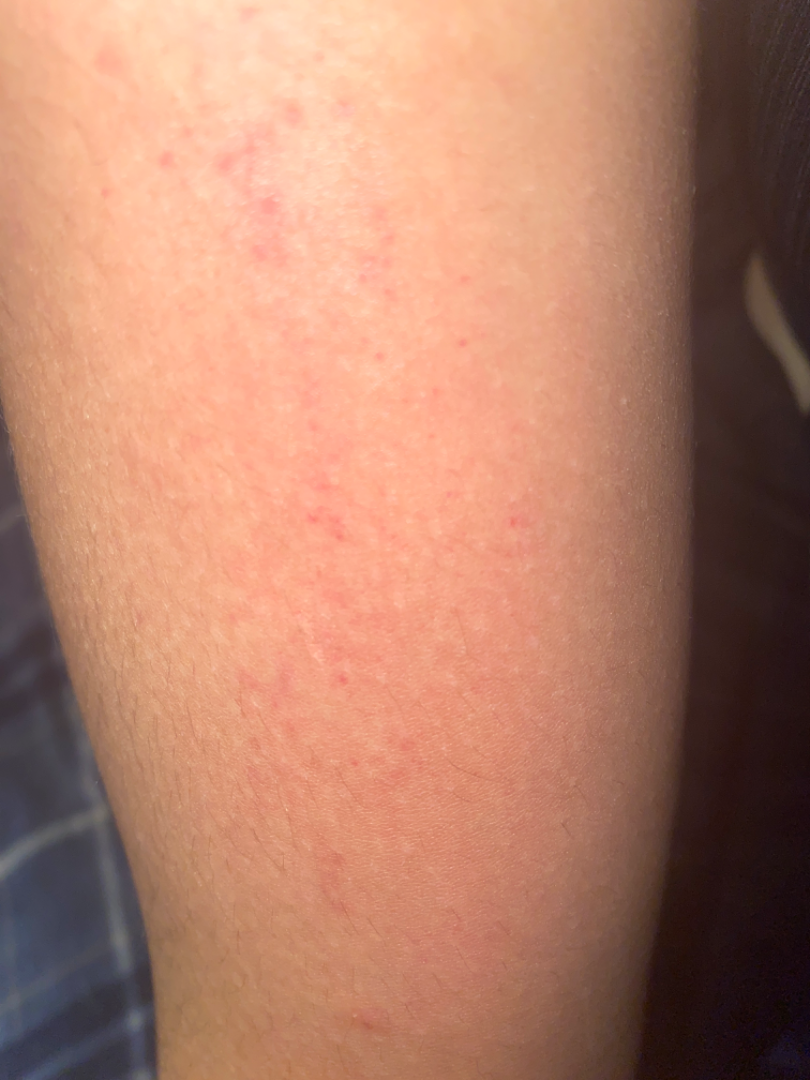– assessment — not assessable